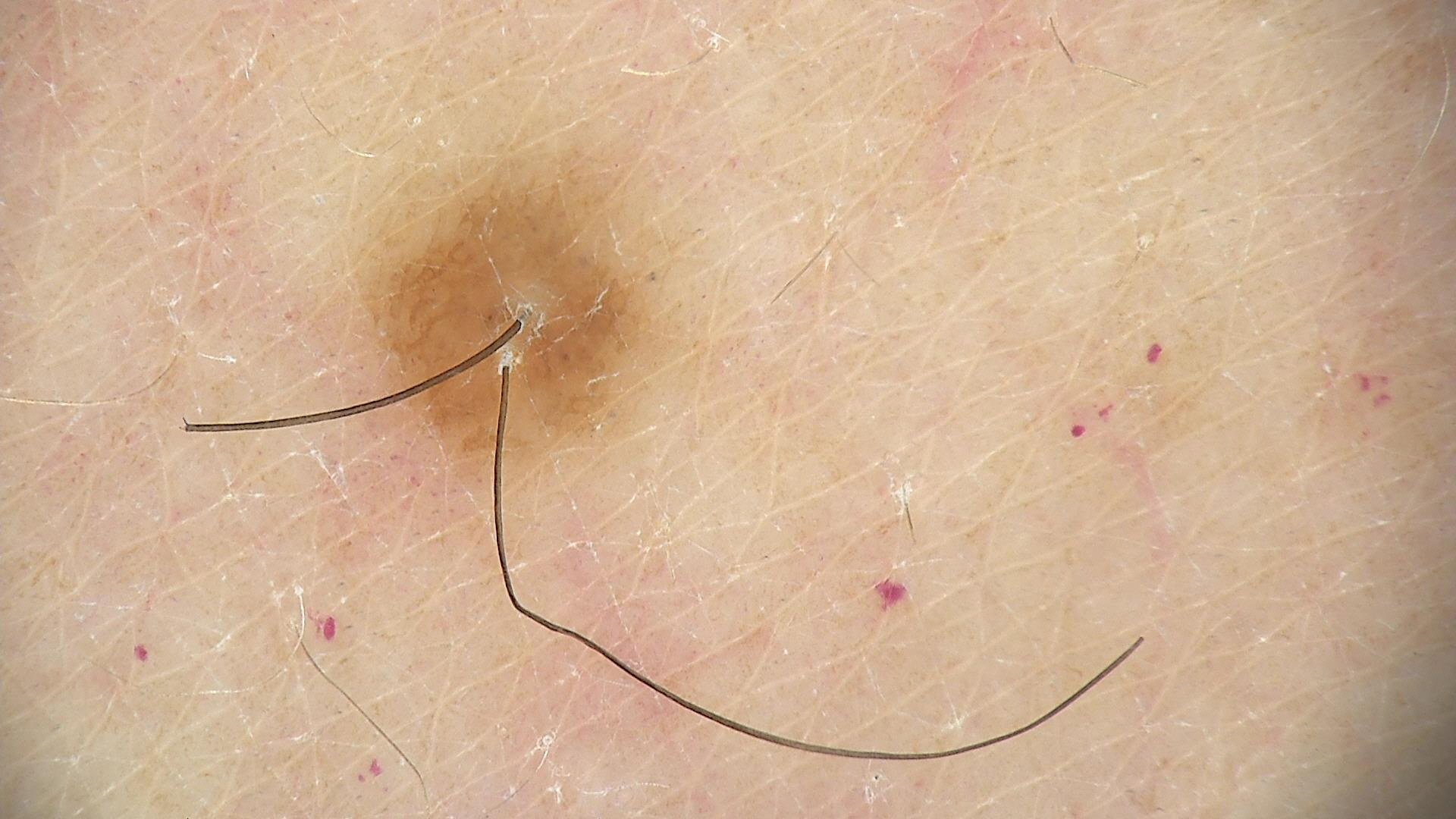Findings:
A dermoscopic image of a skin lesion.
Impression:
Diagnosed as a dermal nevus.